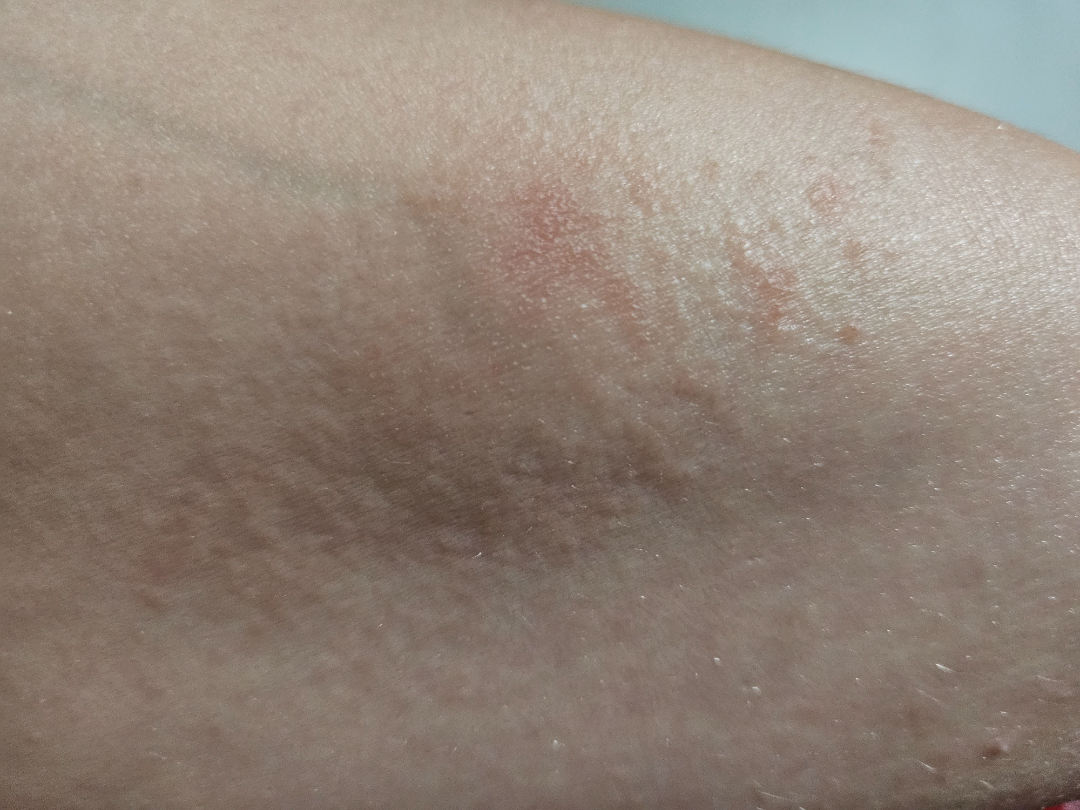Patient information: The patient described the issue as a rash. A close-up photograph. No relevant systemic symptoms. The patient indicates the condition has been present for one to four weeks. The arm is involved. The patient reported no relevant symptoms from the lesion. Review: On teledermatology review, most consistent with Allergic Contact Dermatitis; also raised was Eczema.